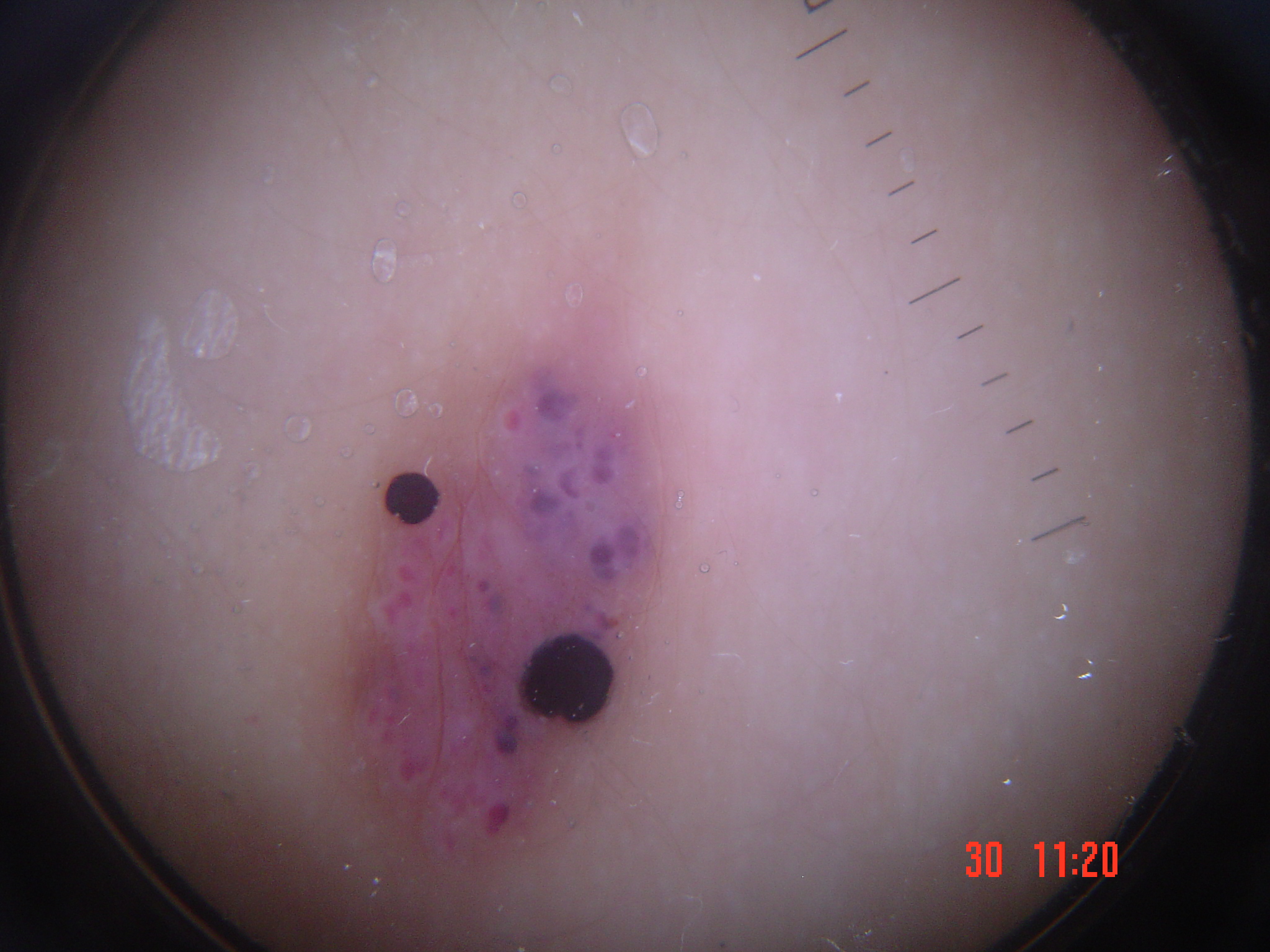A dermoscopy image of a single skin lesion. Classified as a vascular lesion — an angiokeratoma.